A clinical photograph of a skin lesion. A male patient aged 59 — 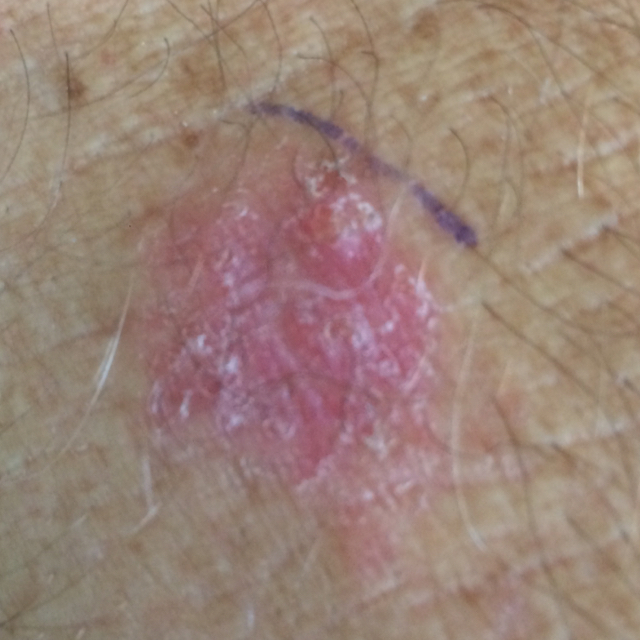Findings:
The lesion was found on the face. The patient reports that the lesion has grown and itches.
Diagnosis:
Confirmed on histopathology as a squamous cell carcinoma.